Fitzpatrick skin type II. Contact-polarized dermoscopy of a skin lesion. A female patient aged 33-37.
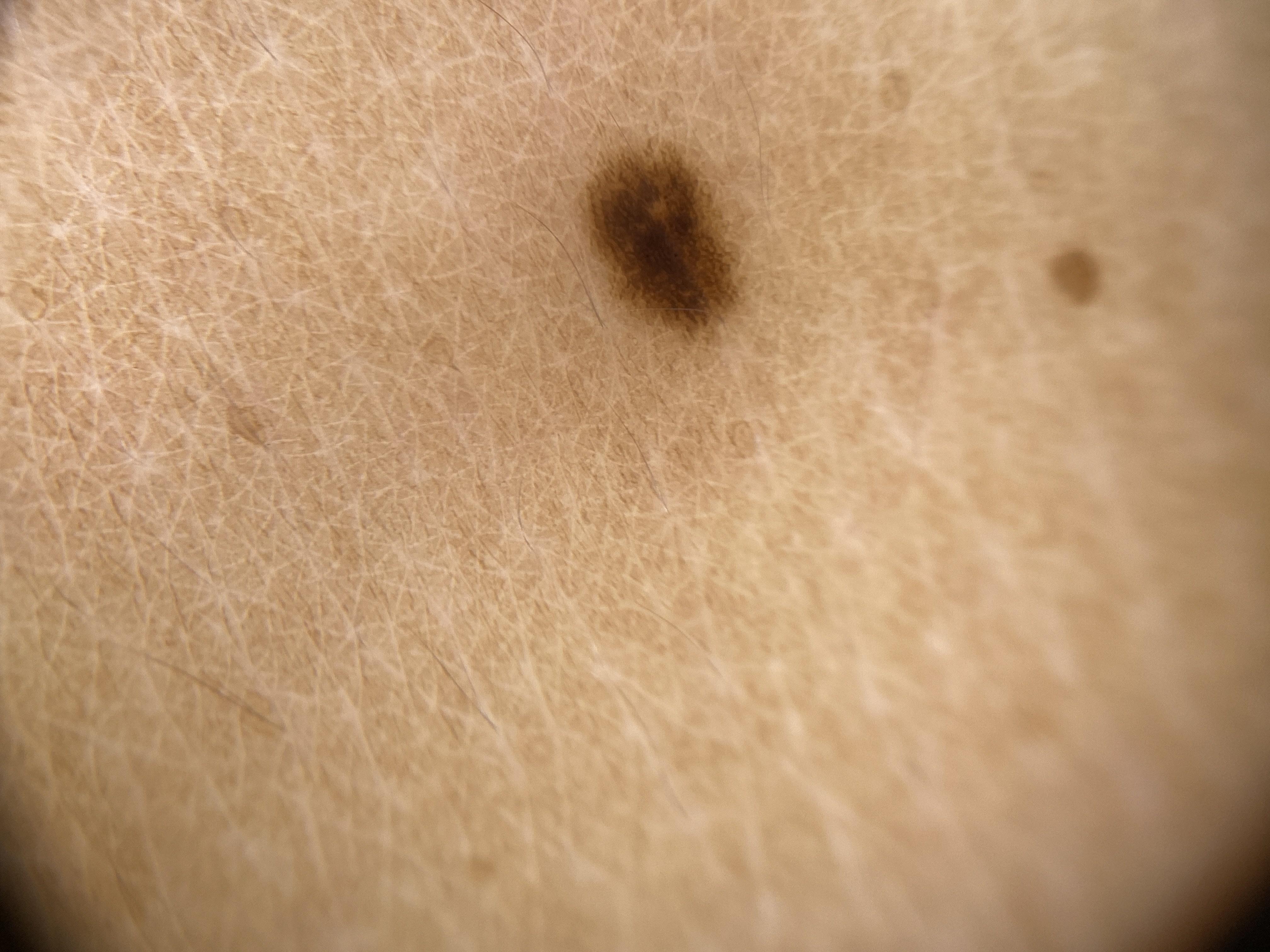<case>
  <lesion_location>
    <region>the trunk</region>
    <detail>the anterior trunk</detail>
  </lesion_location>
  <diagnosis>
    <name>Nevus</name>
    <malignancy>benign</malignancy>
    <confirmation>expert clinical impression</confirmation>
    <lineage>melanocytic</lineage>
  </diagnosis>
</case>